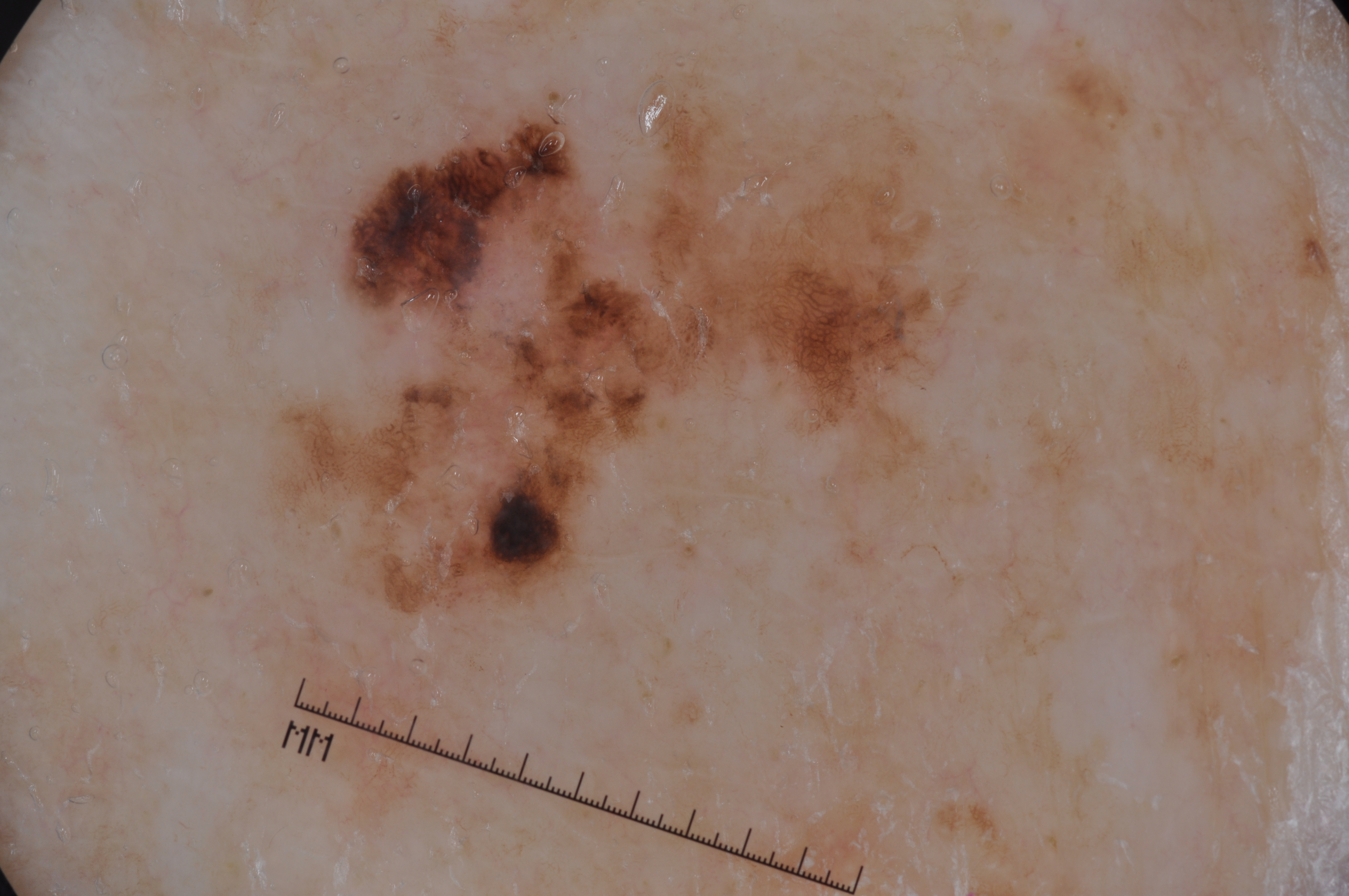Case summary:
A male subject about 85 years old or older. This is a dermoscopic photograph of a skin lesion. With coordinates (x1, y1, x2, y2), lesion location: [274, 105, 948, 609]. The lesion occupies roughly 18% of the field. Dermoscopic review identifies pigment network, with no milia-like cysts, negative network, or streaks.
Diagnosis:
Histopathological examination showed a melanoma, a malignant lesion.